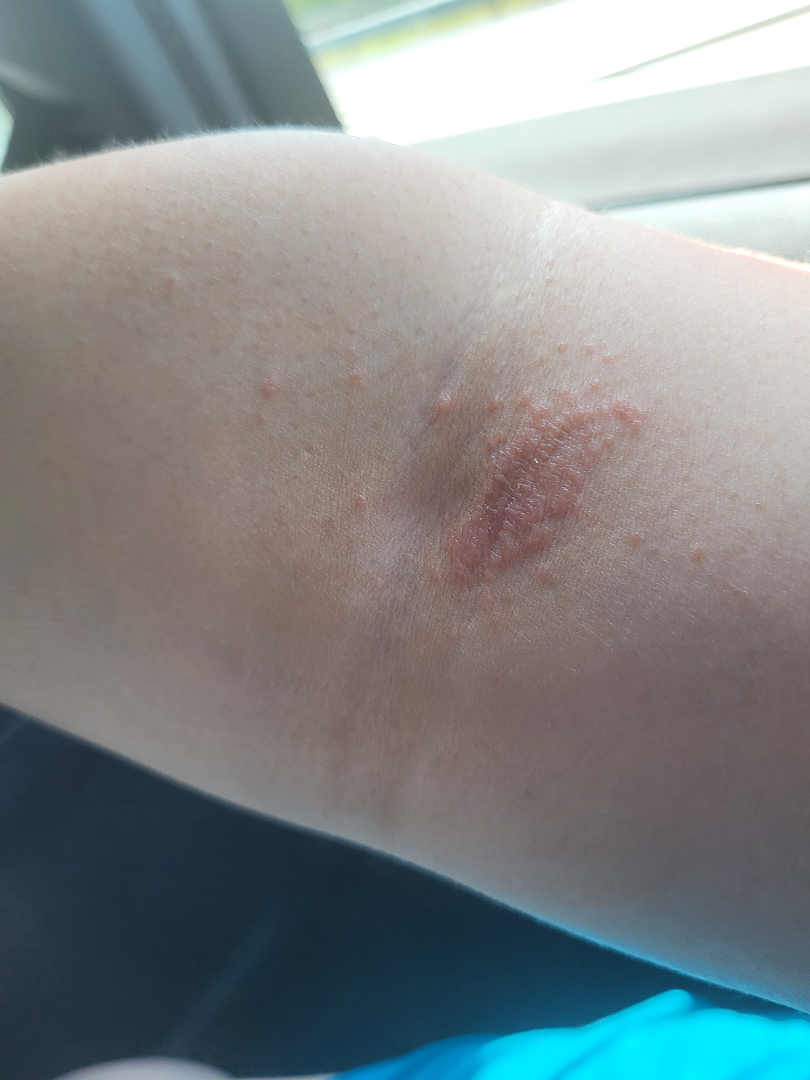Clinical context:
The affected area is the arm. A close-up photograph. Texture is reported as raised or bumpy and rough or flaky. The contributor notes the condition has been present for one to four weeks. Symptoms reported: bothersome appearance, enlargement, darkening, itching and burning. No constitutional symptoms were reported.
Assessment:
Three independent reviewers: the leading impression is Eczema; an alternative is Intertrigo; less likely is Tinea; lower on the differential is Psoriasis.